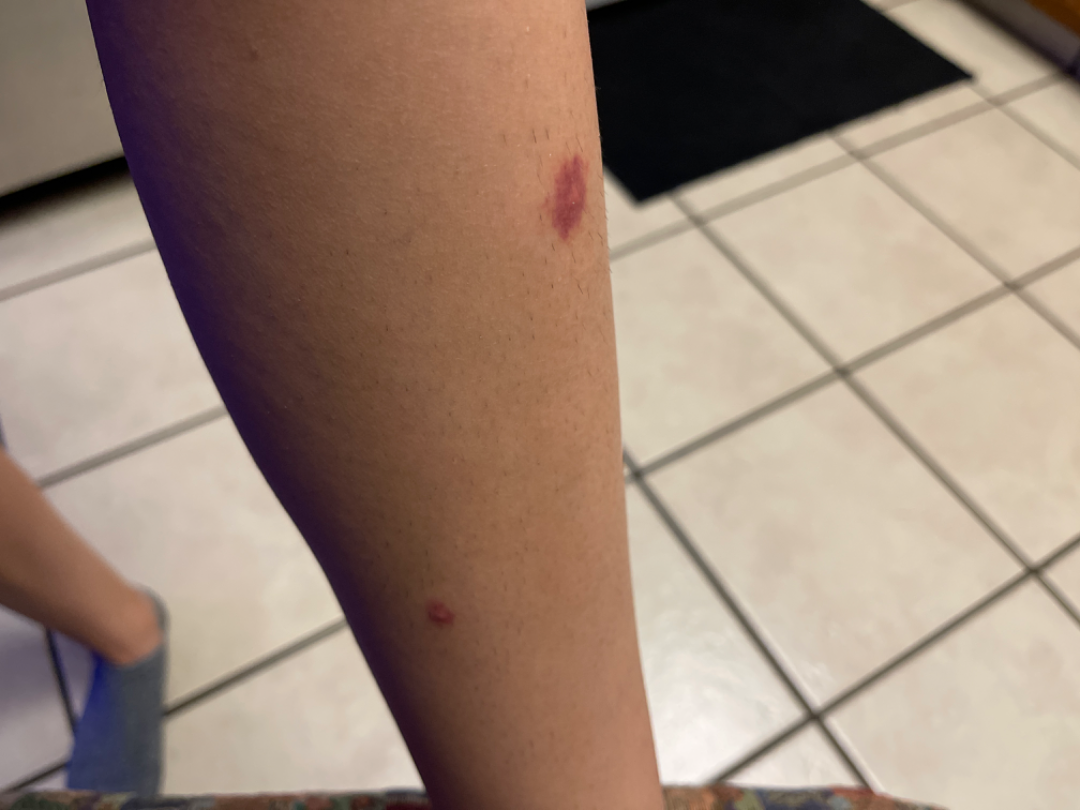Background: Present for about one day. No associated systemic symptoms reported. Texture is reported as flat. Located on the leg. Female contributor, age 18–29. Reported lesion symptoms include burning, bothersome appearance and itching. An image taken at an angle. Self-categorized by the patient as a rash. Findings: Purpura (leading); Insect Bite (considered); Benign cutaneous vascular tumor (unlikely); Pigmented purpuric eruption (unlikely).